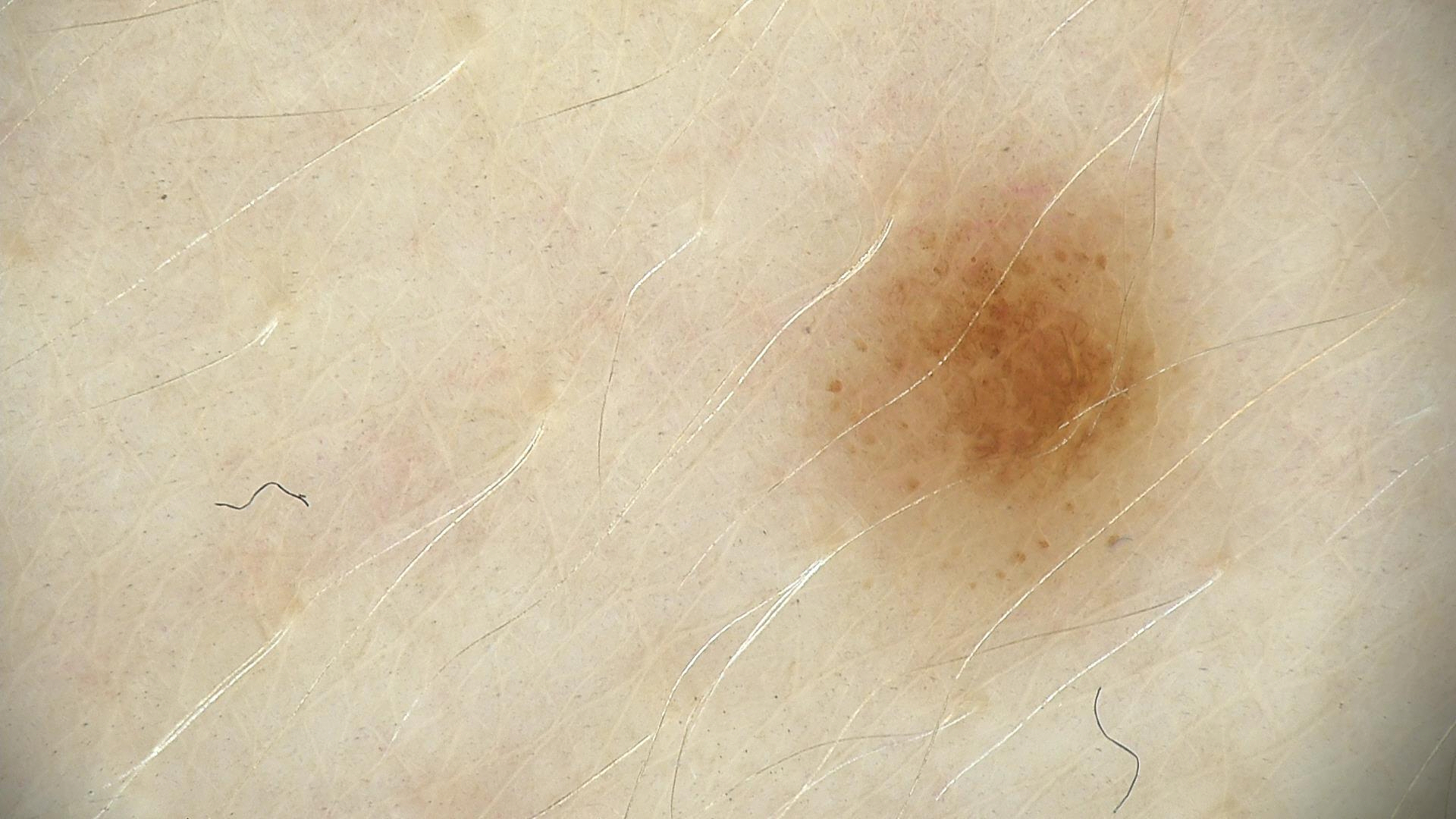Dermoscopy of a skin lesion.
Diagnosed as a dysplastic junctional nevus.